A dermoscopic photograph of a skin lesion.
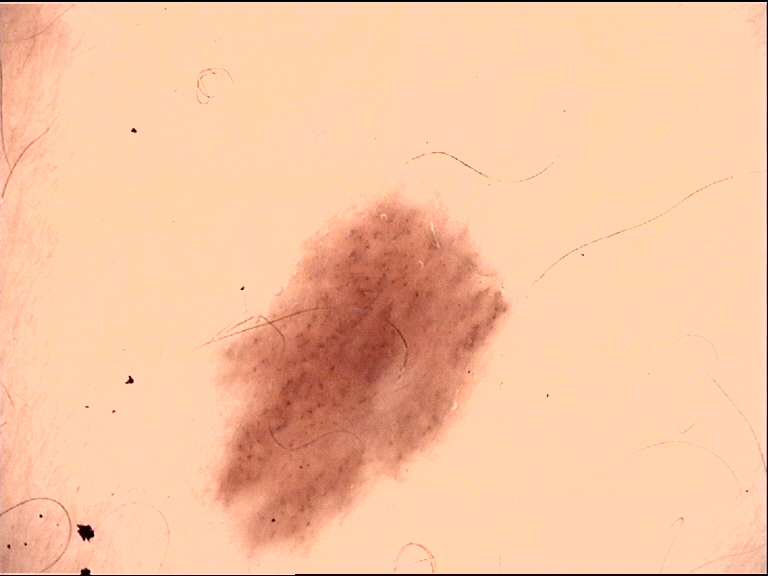label: dysplastic junctional nevus (expert consensus)